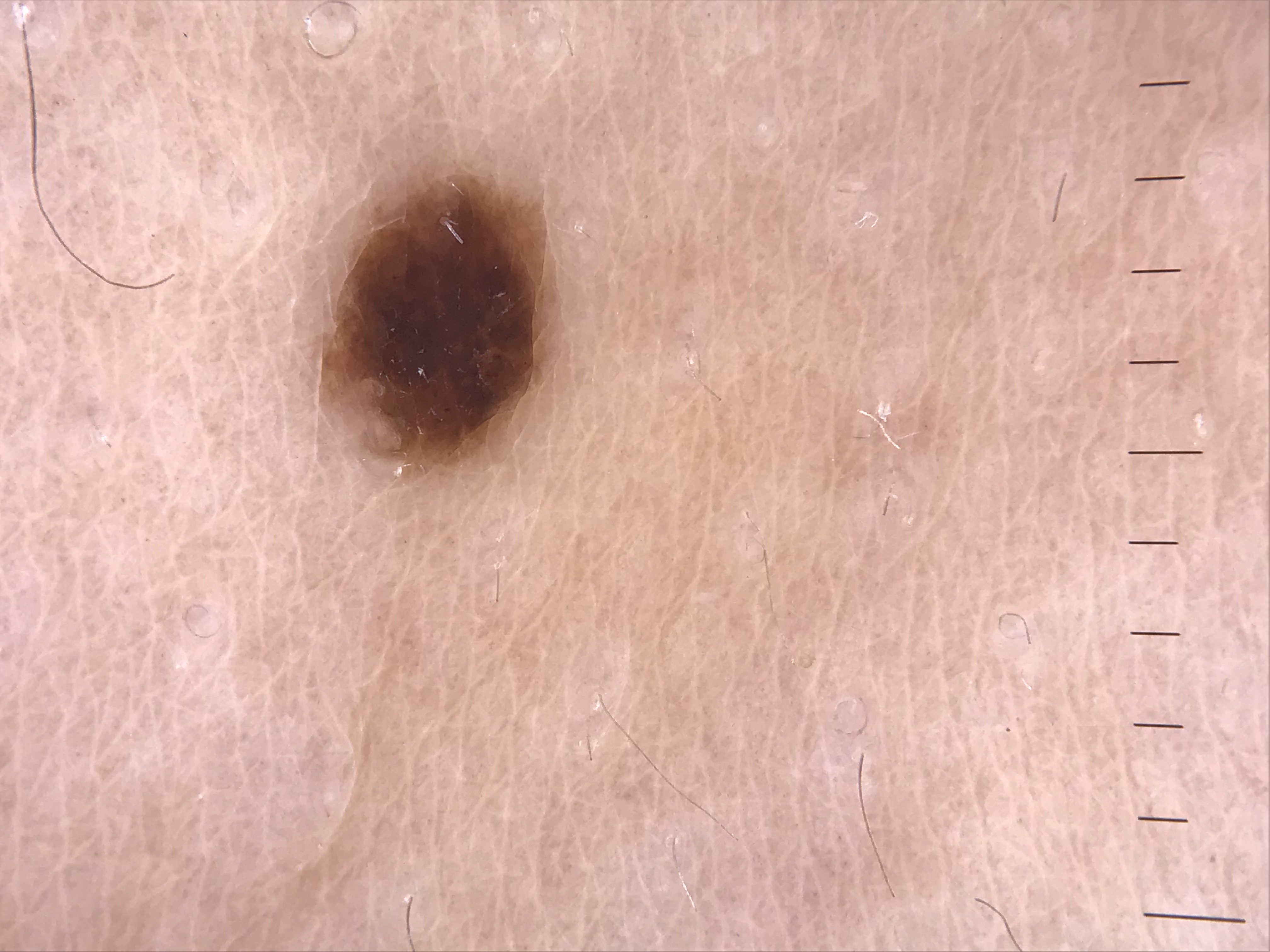Classified as a junctional nevus.